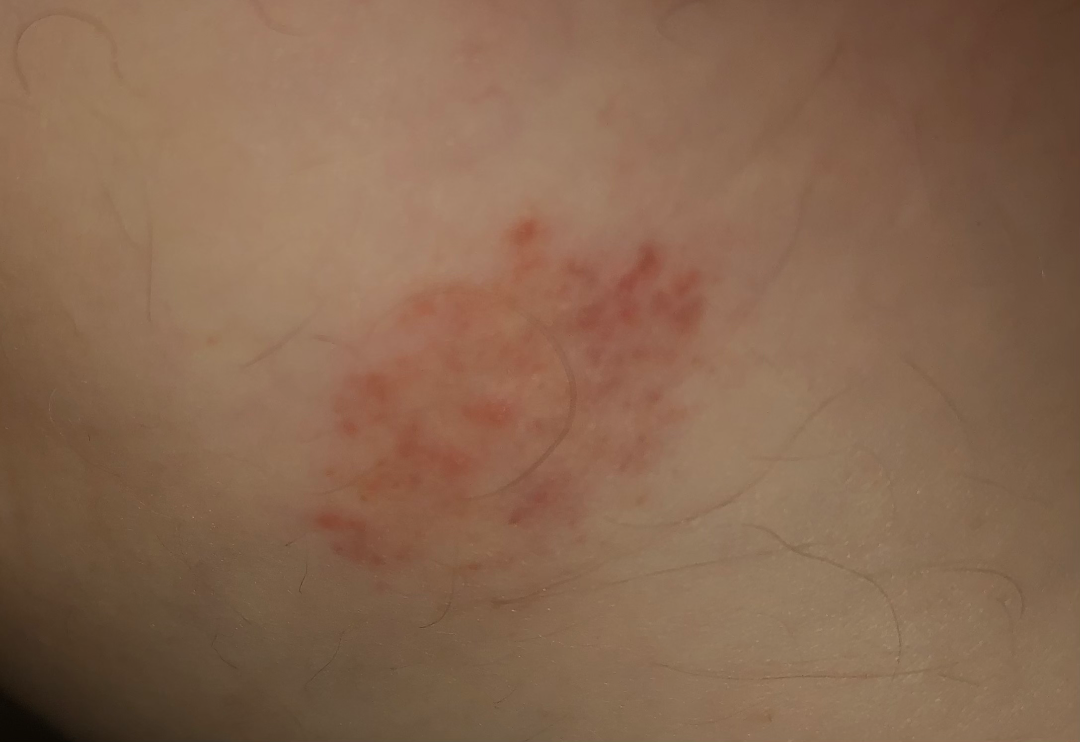Impression:
The dermatologist could not determine a likely condition from the photograph alone.
History:
This is a close-up image.